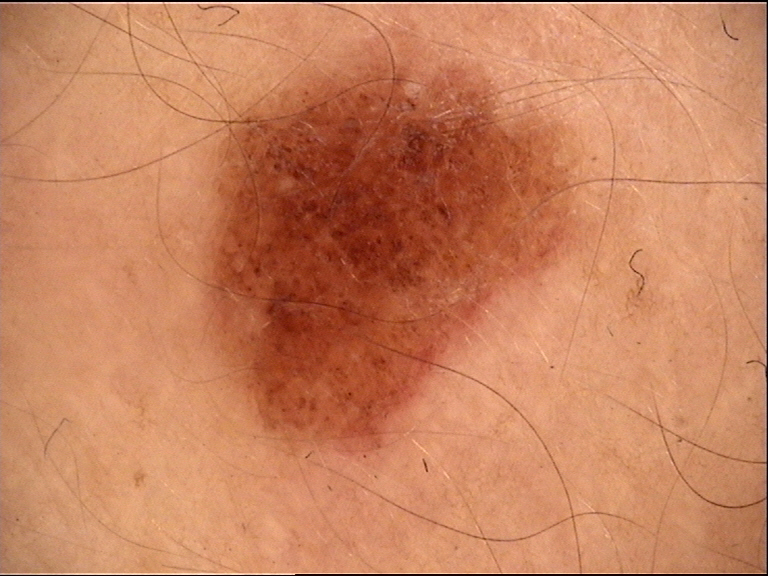Summary:
A dermoscopic photograph of a skin lesion. The morphology is that of a banal lesion.
Impression:
Classified as a compound nevus.